The leg is involved · this is a close-up image — 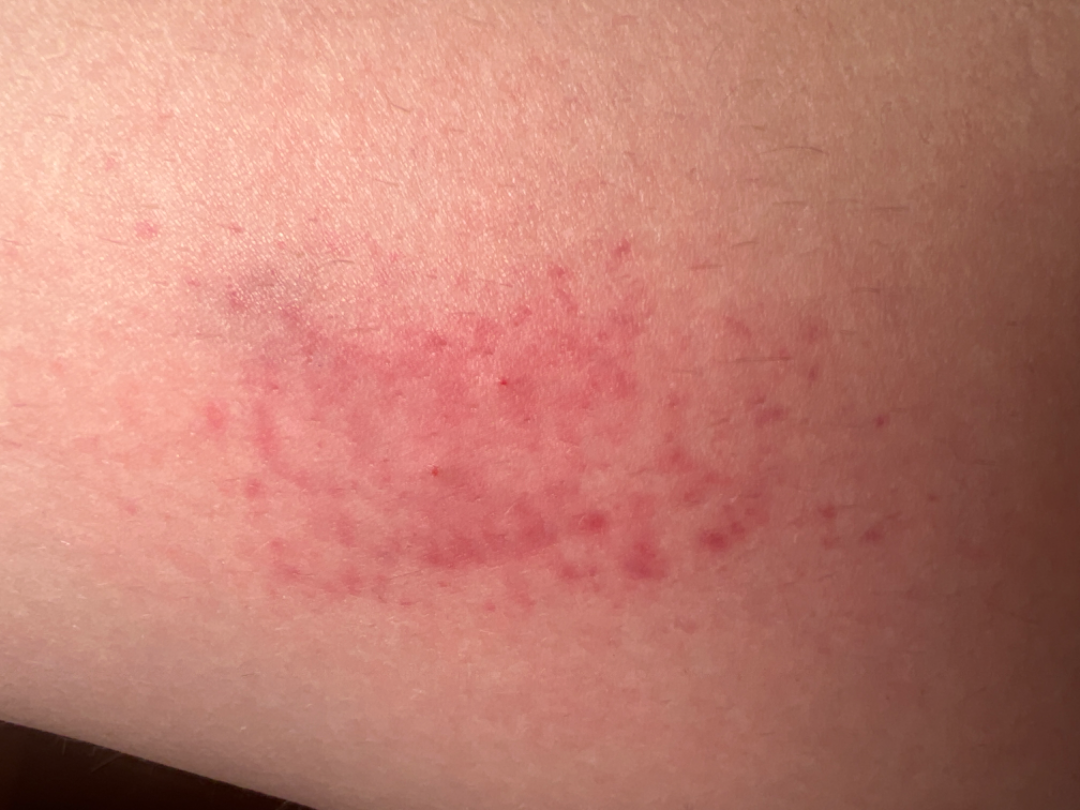| feature | finding |
|---|---|
| assessment | not assessable |
| systemic symptoms | none reported |
| patient-reported symptoms | itching |
| texture | flat |
| onset | about one day |
| patient's own categorization | a rash |